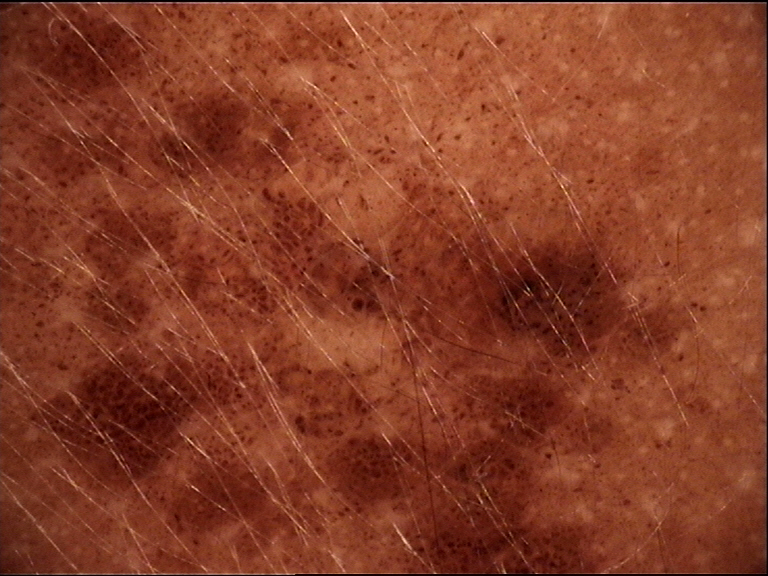class — congenital junctional nevus (expert consensus)